A close-up photograph — 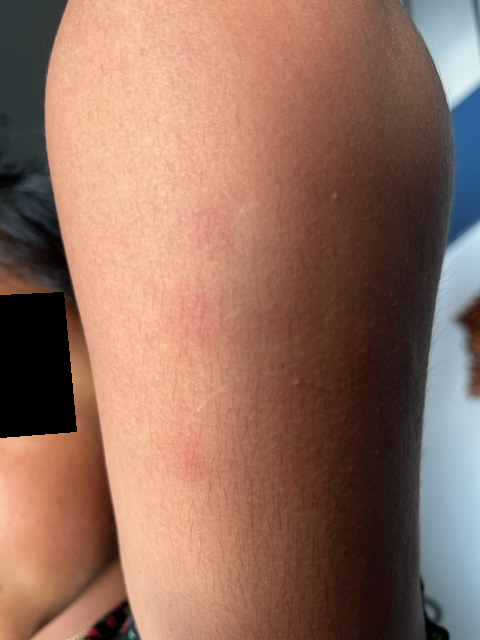Diagnostic features were not clearly distinguishable in this photograph.